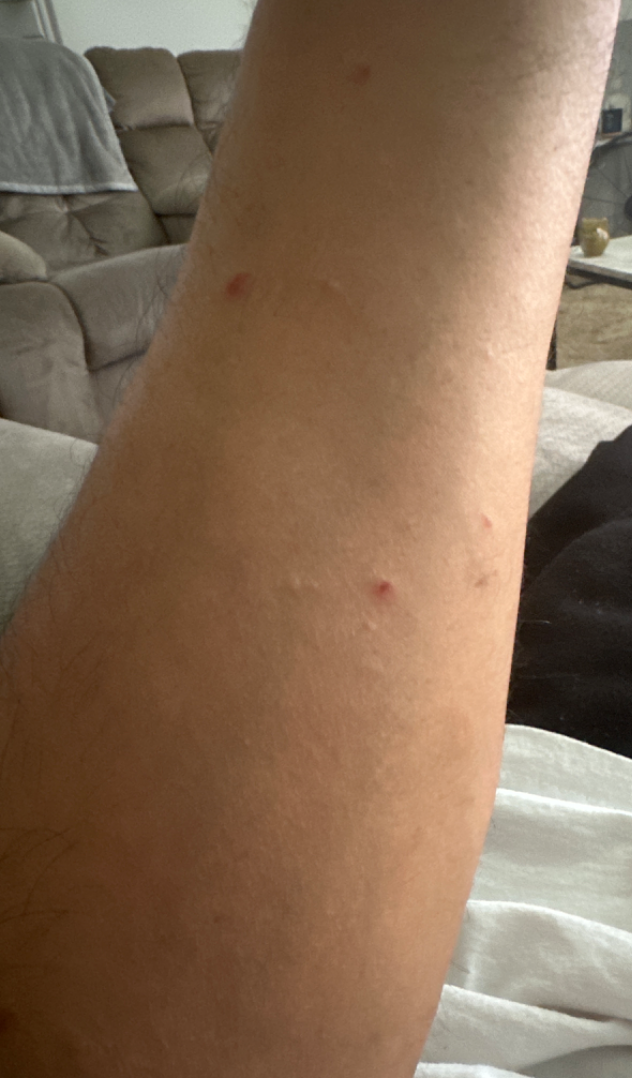Notes:
• dermatologist impression — the favored diagnosis is Acute constitutional eczema; also consider Infestation caused by Sarcoptes scabiei var bovis